Located on the arm and leg, this image was taken at a distance: 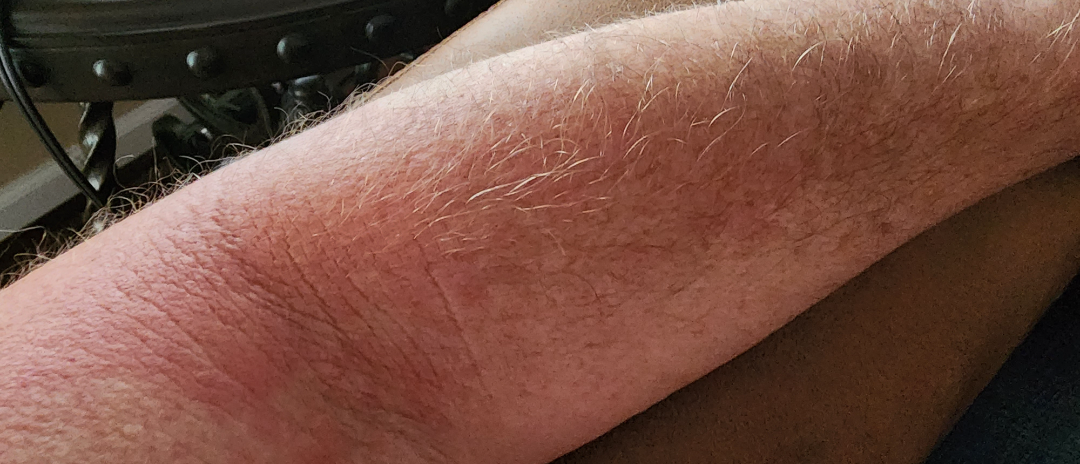– assessment · unable to determine